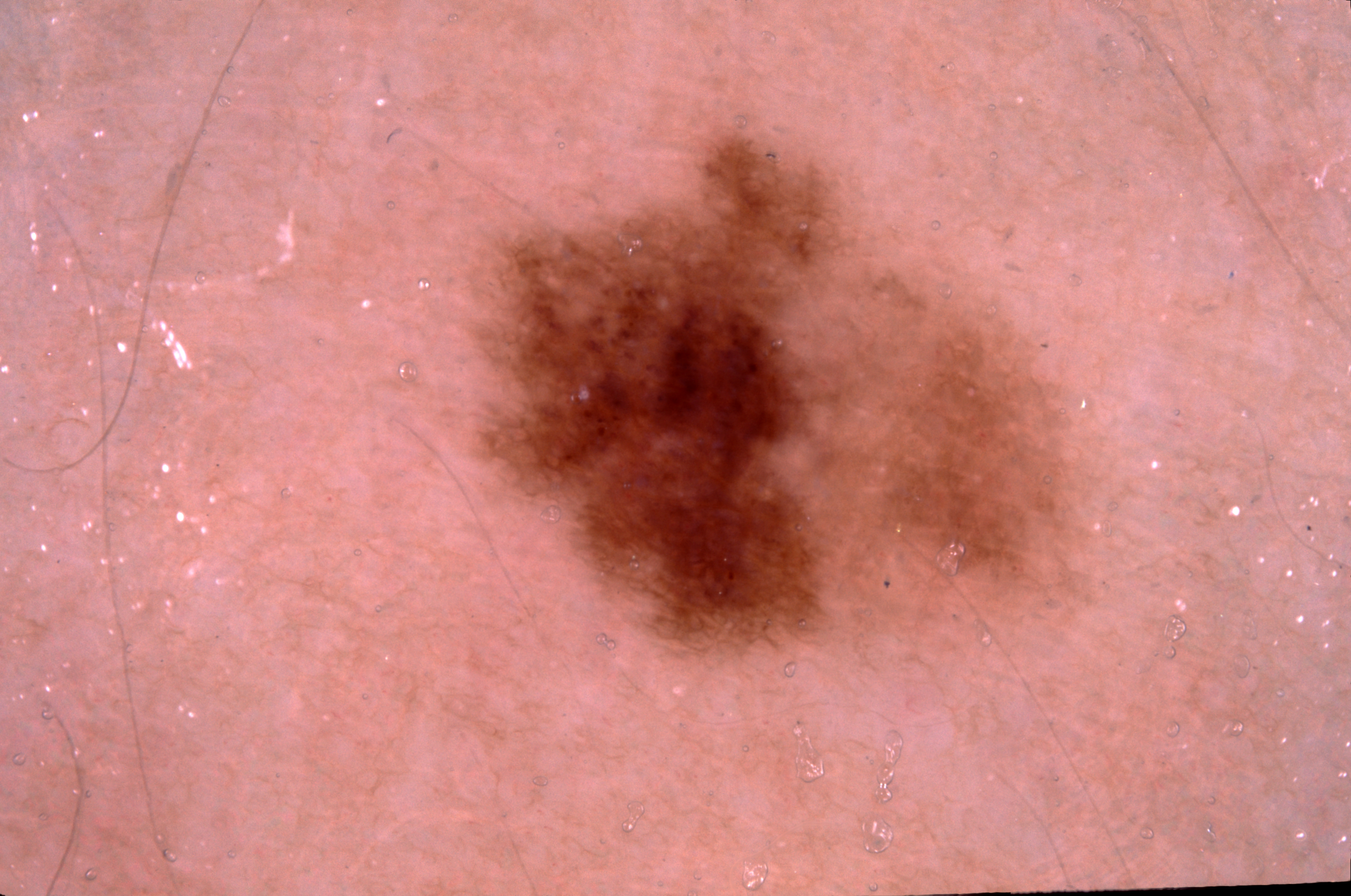Summary: A dermoscopy image of a single skin lesion. Dermoscopic assessment notes pigment network. As (left, top, right, bottom), the lesion spans box(434, 67, 1109, 698). A moderately sized lesion. Conclusion: Diagnosed as a melanocytic nevus.